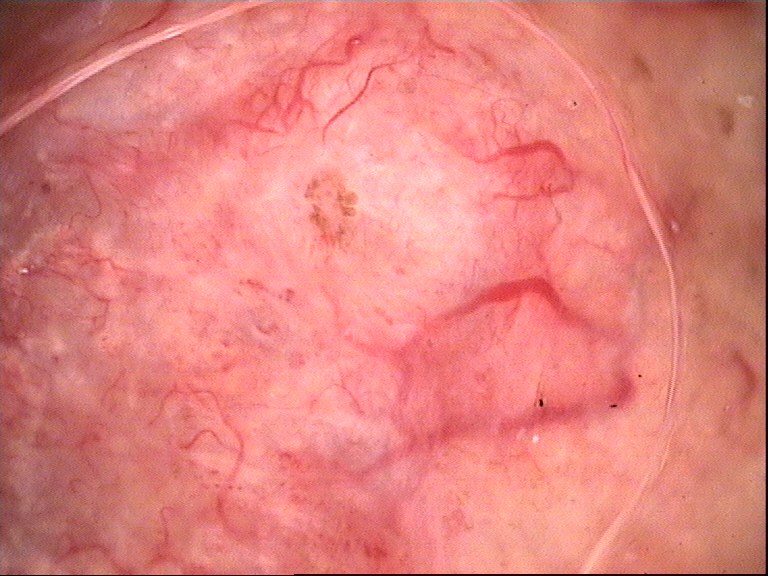A dermoscopic image of a skin lesion. The biopsy diagnosis was a keratinocytic, malignant lesion — a basal cell carcinoma.